This is a close-up image: 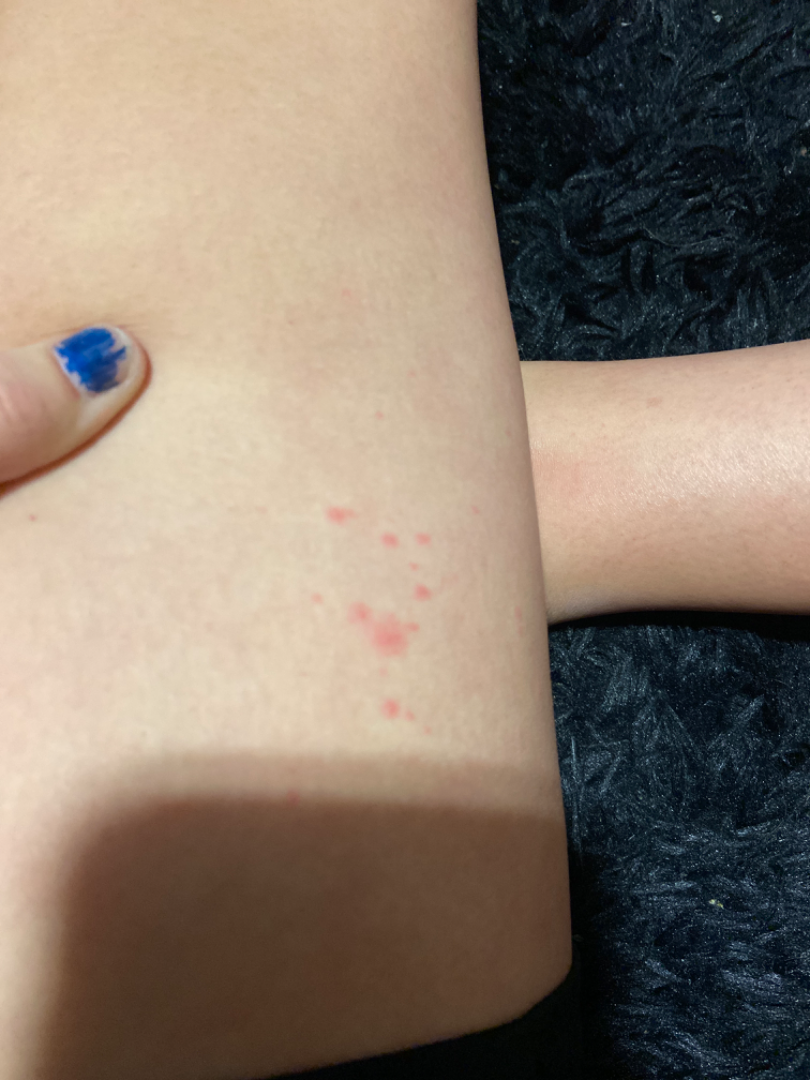Impression: On remote dermatologist review, Urticaria (possible); Insect Bite (possible); Hypersensitivity (possible).